A dermoscopy image of a single skin lesion: 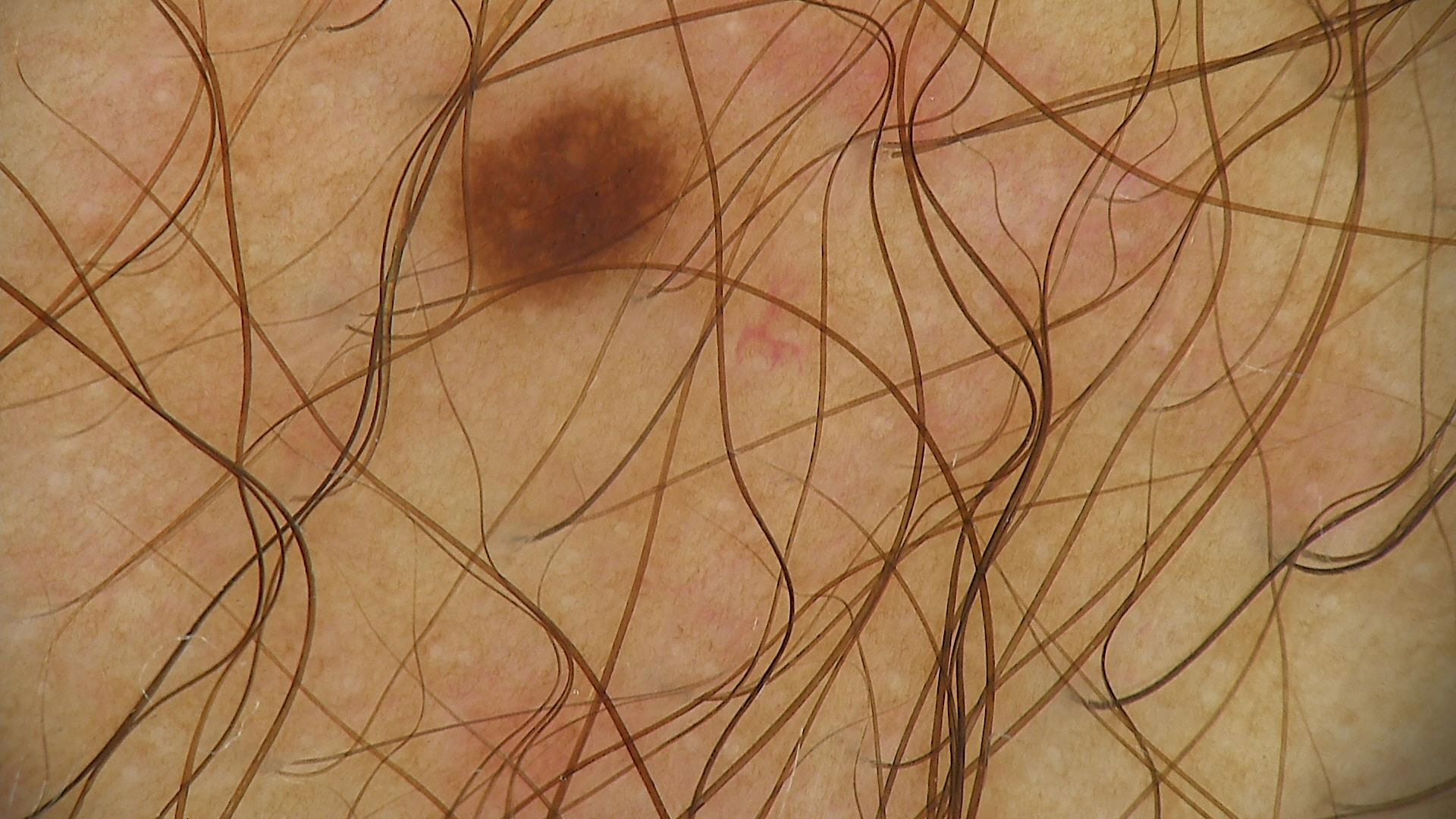Consistent with a dysplastic junctional nevus.